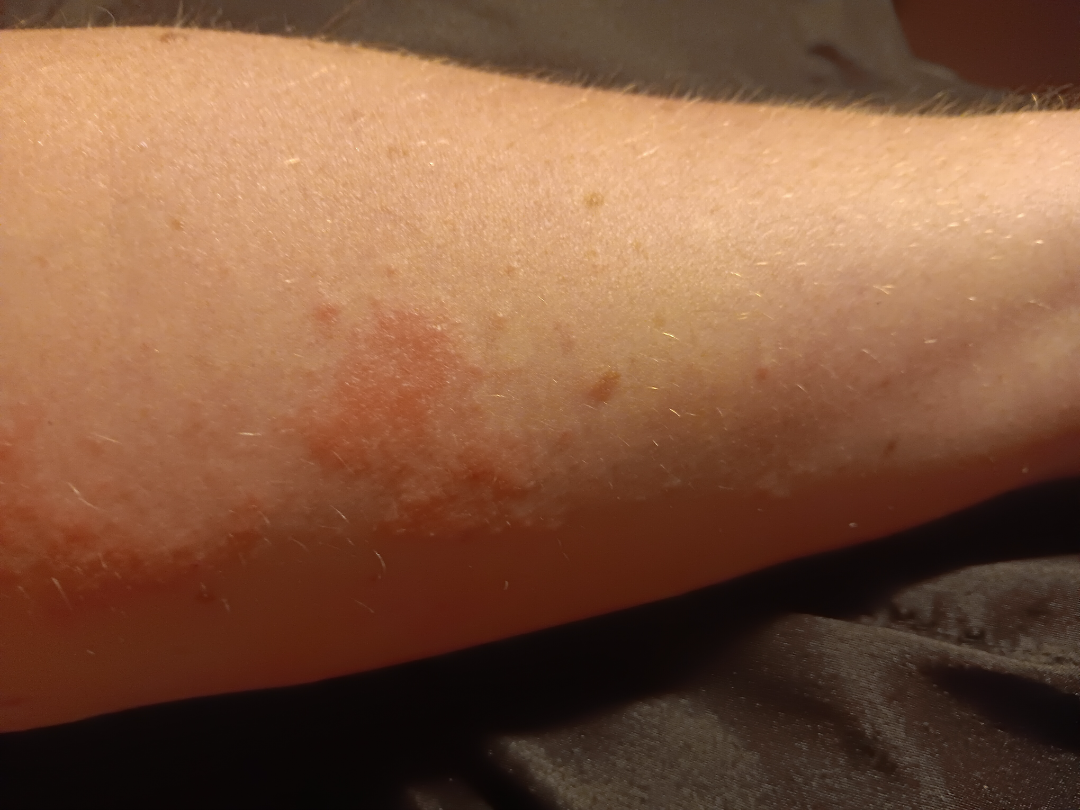Review: The skin condition could not be confidently assessed from this image. Patient information: The patient reports the condition has been present for one to three months. Texture is reported as raised or bumpy. A close-up photograph. The patient considered this a rash. The patient reports enlargement and itching. The affected area is the arm. No relevant systemic symptoms. Fitzpatrick phototype II.